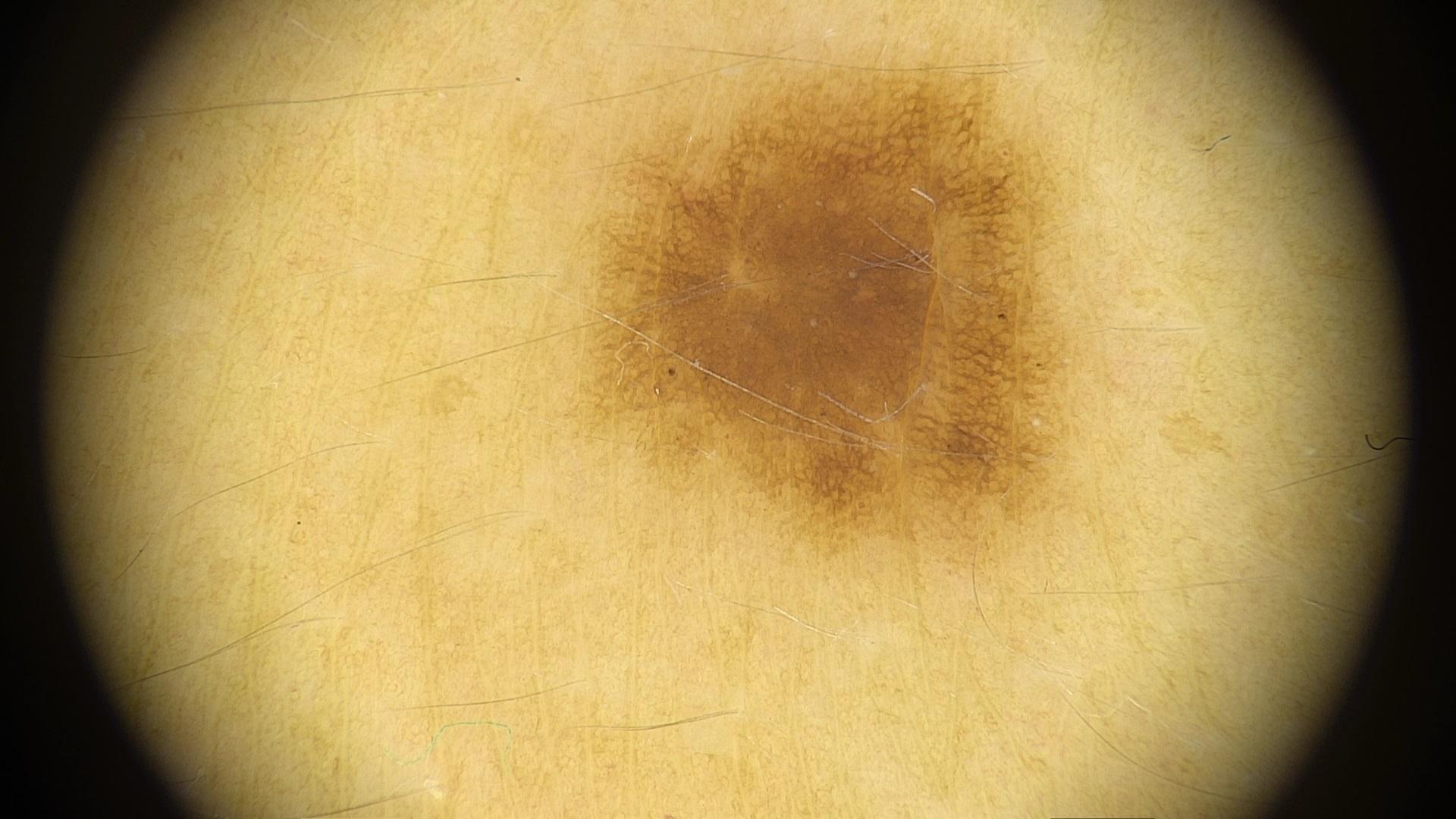{"image": "dermatoscopic image", "patient": {"age_approx": 35, "sex": "female"}, "lesion_location": {"region": "the trunk", "detail": "the posterior trunk"}, "diagnosis": {"name": "Nevus", "malignancy": "benign", "confirmation": "expert clinical impression", "lineage": "melanocytic"}}